An image taken at an angle · the top or side of the foot is involved: 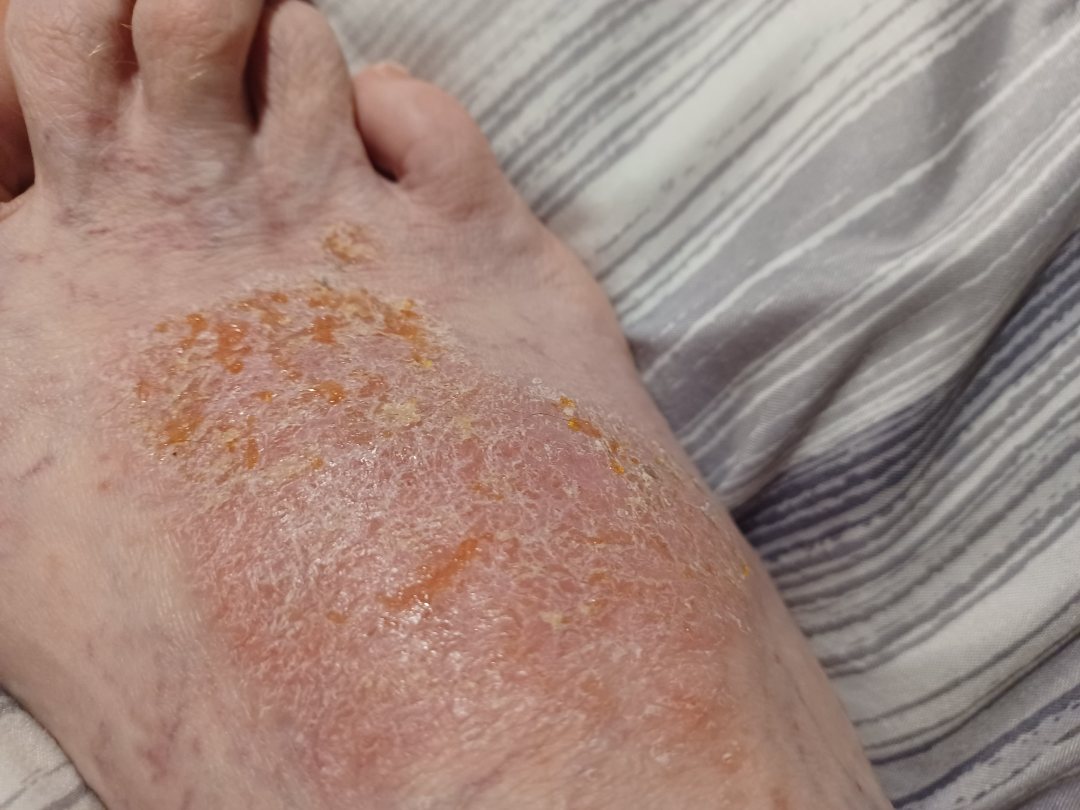Case summary:
- skin tone — Fitzpatrick skin type II; lay reviewers estimated Monk skin tone scale 3 (US pool) or 2 (India pool)
- symptom duration — three to twelve months
- self-categorized as — a rash
- patient-reported symptoms — pain, bothersome appearance, burning, bleeding, darkening, itching and enlargement
- associated systemic symptoms — none reported
- diagnostic considerations — a single dermatologist reviewed the case: most consistent with Allergic Contact Dermatitis; the differential also includes Impetigo; possibly Irritant Contact Dermatitis